The photo was captured at an angle · the lesion is associated with bothersome appearance, burning, pain and enlargement · texture is reported as rough or flaky, raised or bumpy, flat and fluid-filled · the affected area is the leg · present for one to three months · the subject is a female aged 60–69:
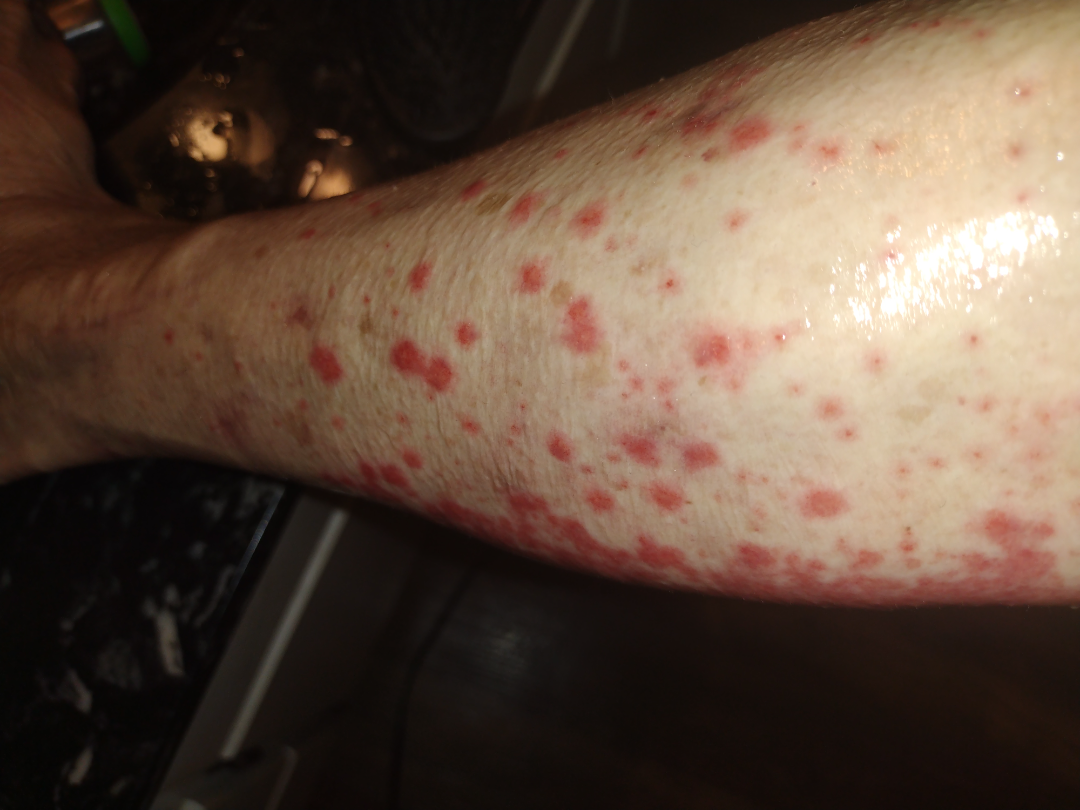impression = Leukocytoclastic Vasculitis and Cellulitis were each considered, in no particular order; possibly Impetigo